A male subject 71 years old; Fitzpatrick phototype III; a clinical photograph showing a skin lesion; the chart records prior skin cancer (patient or family), pesticide exposure, and prior malignancy (patient or family) — 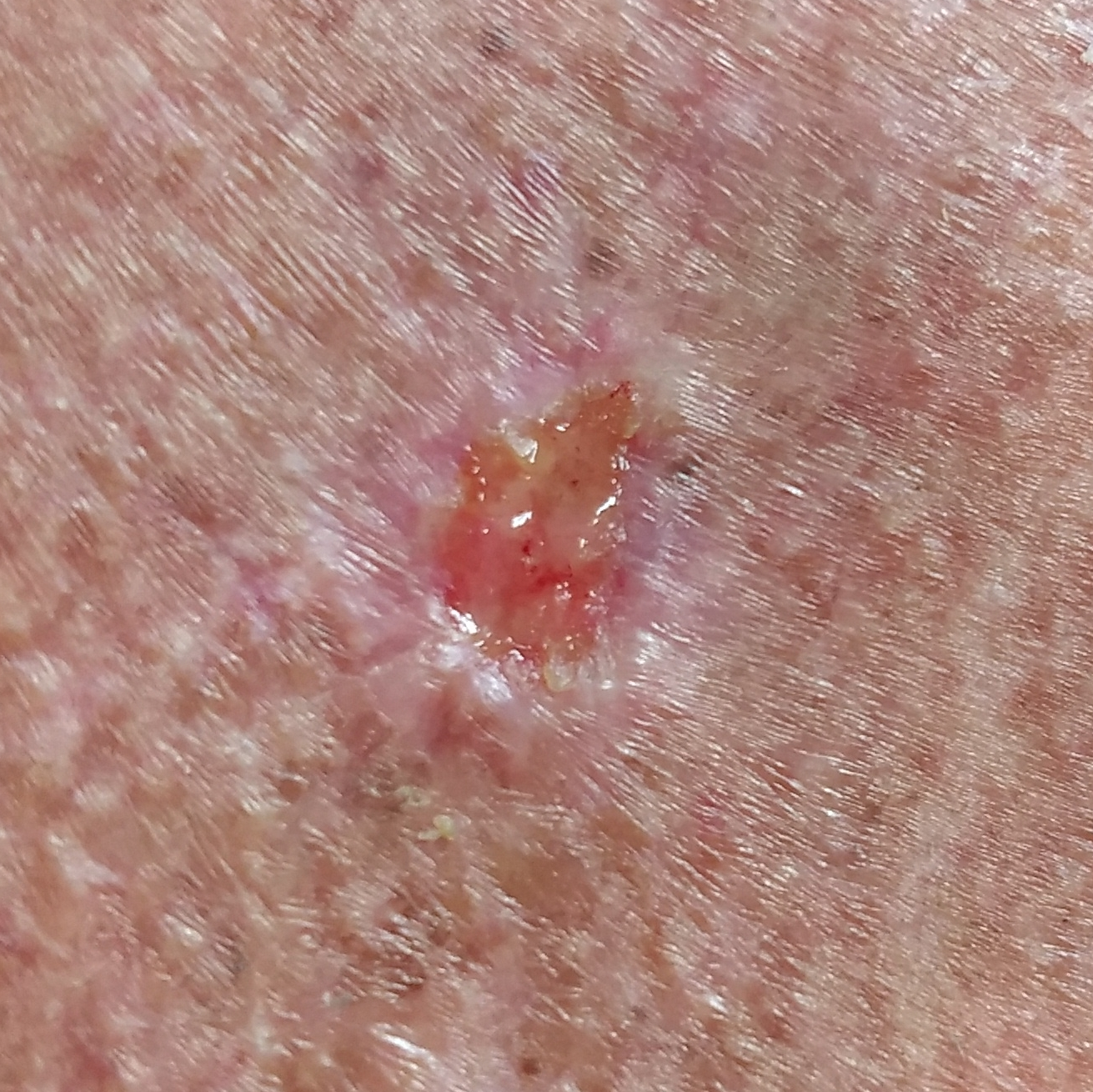{"lesion_location": "the chest", "symptoms": {"present": ["elevation", "itching", "bleeding", "pain", "growth"], "absent": ["change in appearance"]}, "diagnosis": {"name": "basal cell carcinoma", "code": "BCC", "malignancy": "malignant", "confirmation": "histopathology"}}